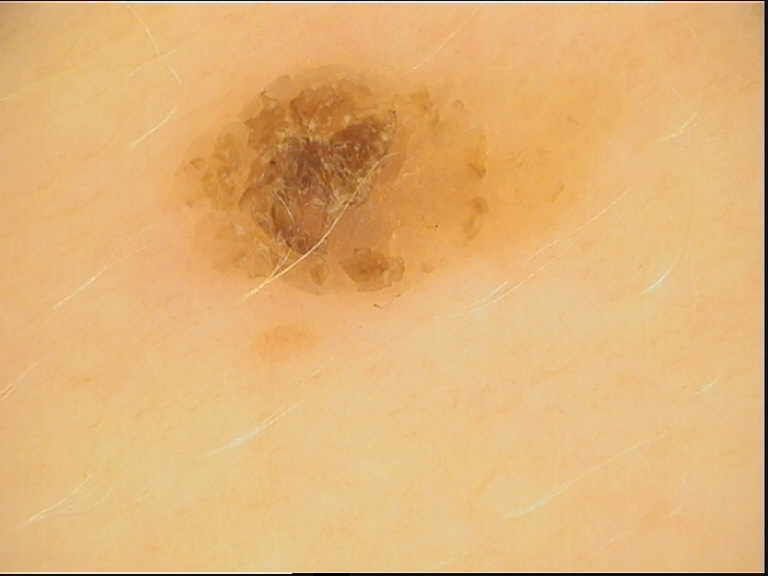Impression:
Labeled as a seborrheic keratosis.